A macroscopic clinical photograph of a skin lesion · acquired for a research image collection, with no referral diagnosis · a male patient aged 62:
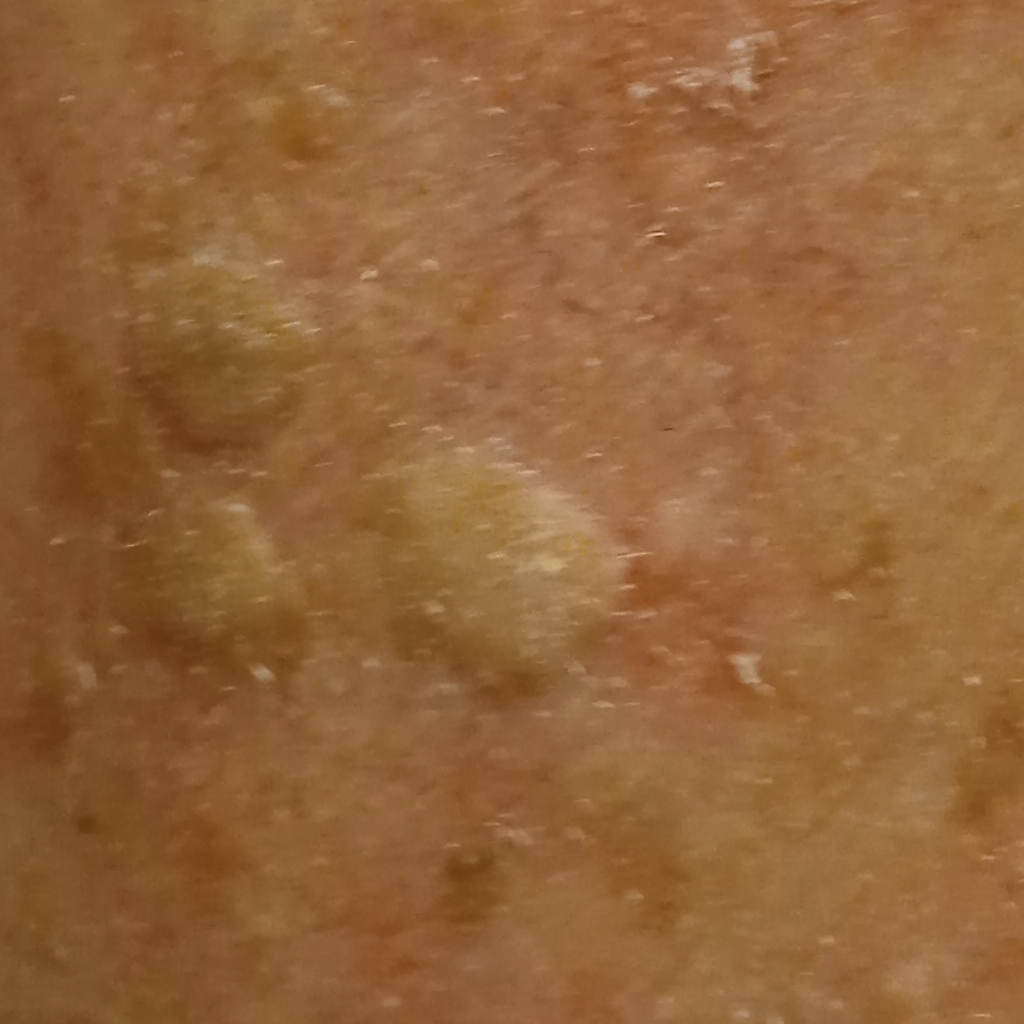Case summary: The lesion is located on the face. The lesion measures approximately 7.5 mm. Conclusion: The dermatologists' assessment was a seborrheic keratosis.